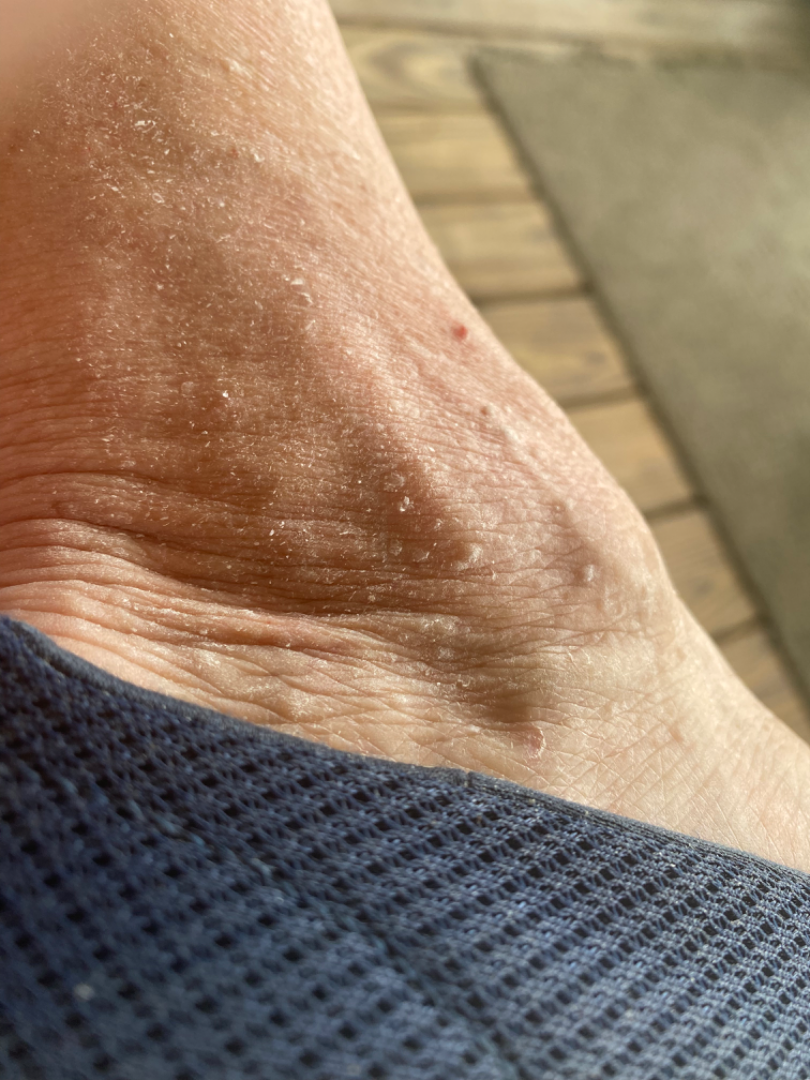History: The leg is involved. Texture is reported as raised or bumpy. This image was taken at an angle. Reported duration is one to four weeks.